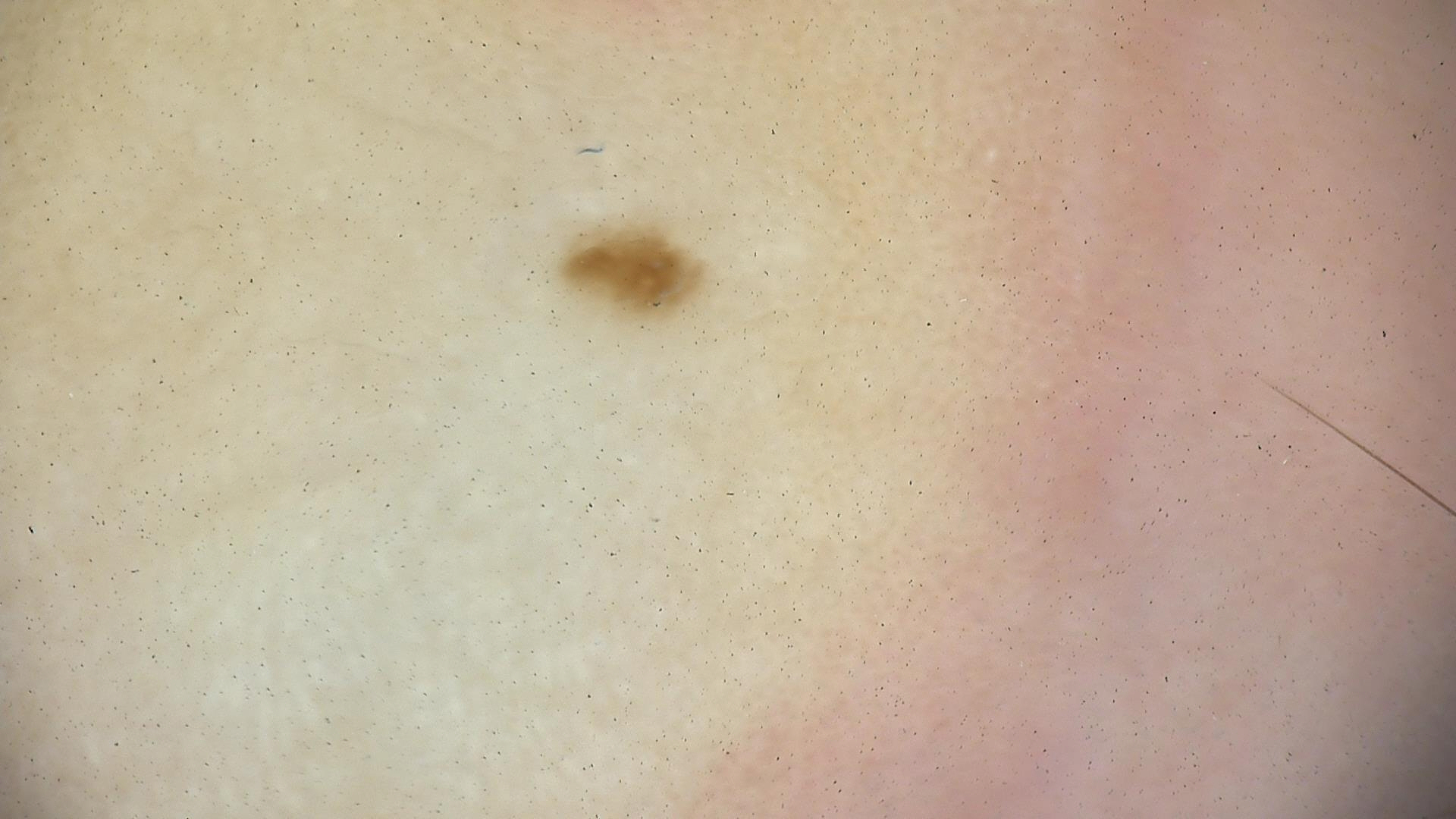diagnostic label — dysplastic junctional nevus (expert consensus).